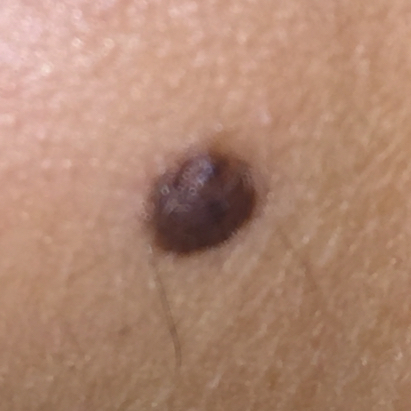Conclusion:
Consistent with a nevus.